The patient is a female aged 18–29. Close-up view. The arm is involved:
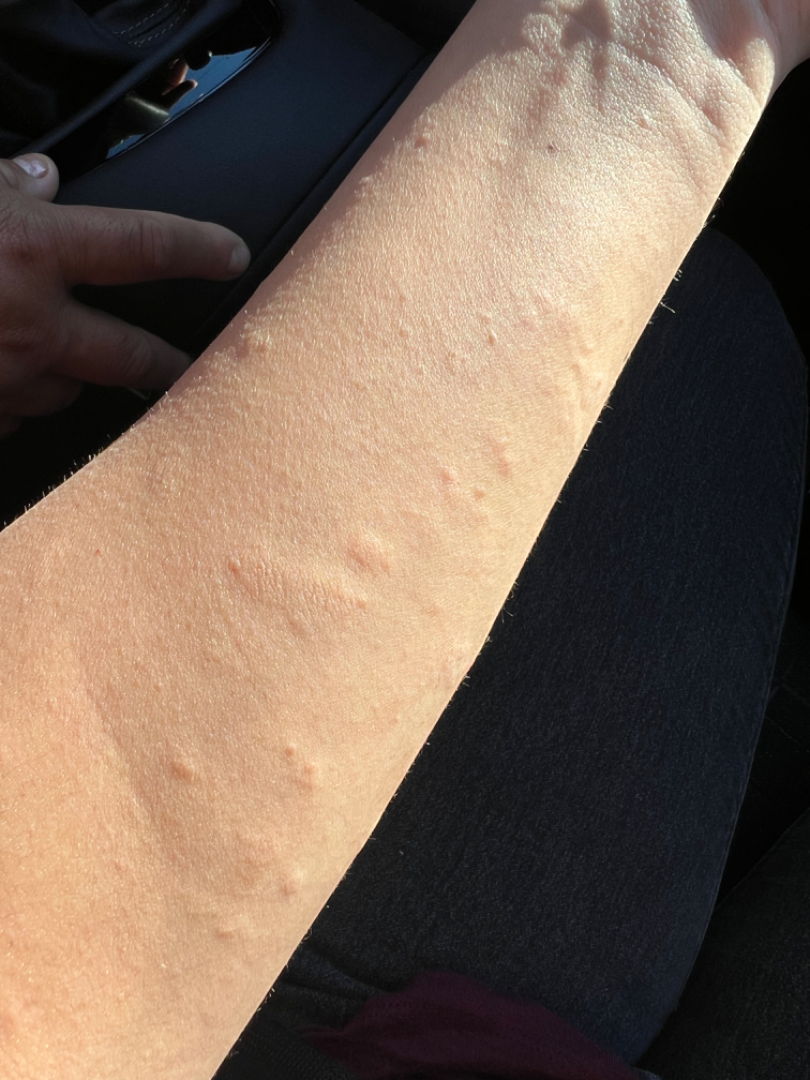History: The contributor reports the lesion is flat and raised or bumpy. The condition has been present for one to four weeks. Impression: Reviewed remotely by one dermatologist: favoring Urticaria; an alternative is Acute and chronic dermatitis.